A clinical photo of a skin lesion taken with a smartphone:
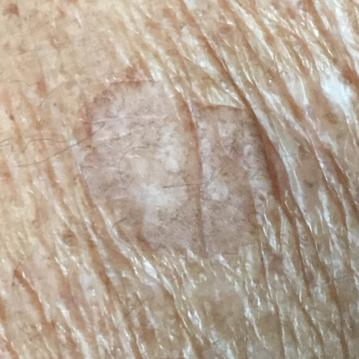body site: an arm
patient-reported symptoms: itching, elevation
impression: seborrheic keratosis (clinical consensus)